A dermoscopy image of a single skin lesion.
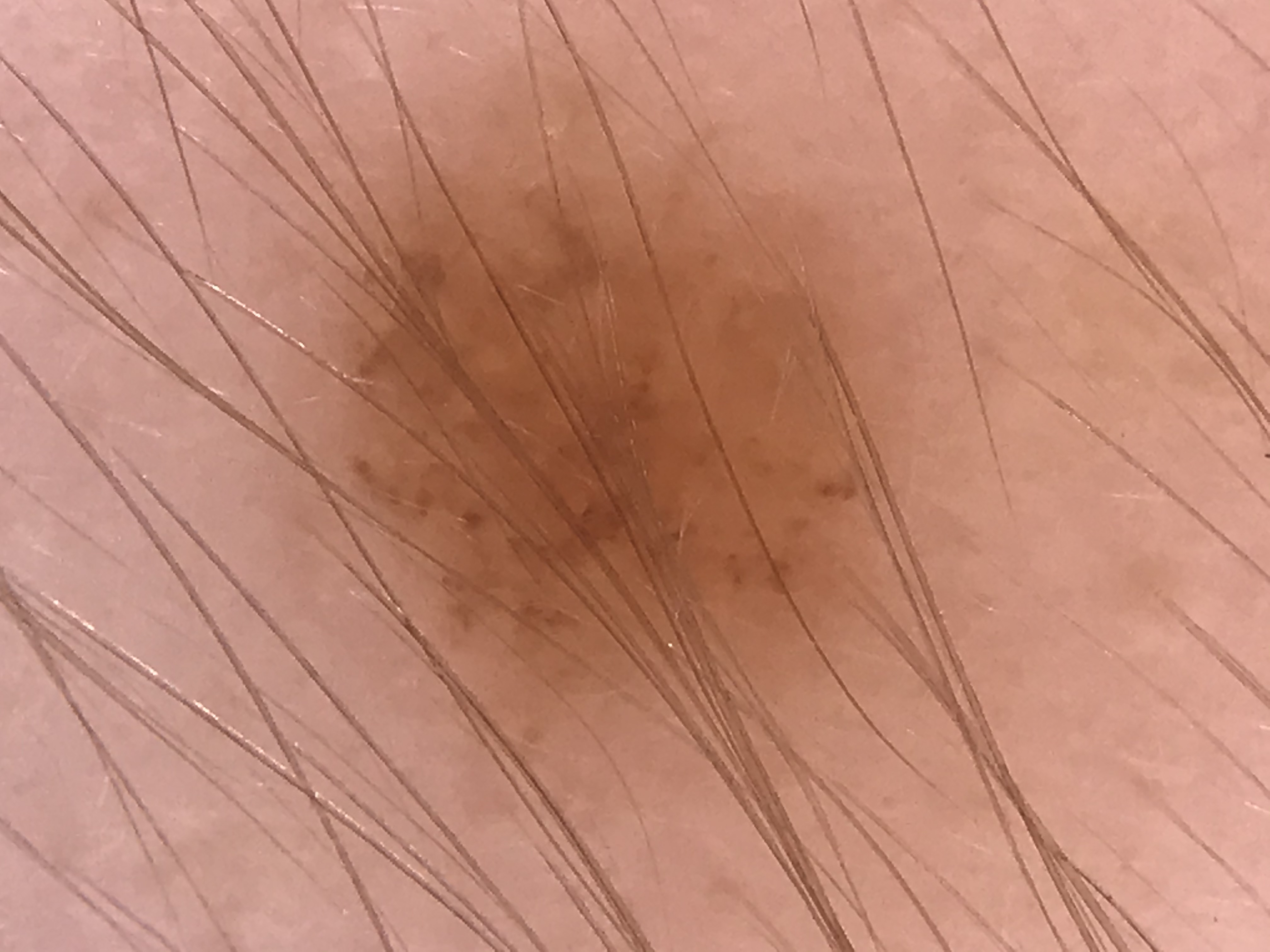Consistent with a banal lesion — a compound nevus.